Reported duration is less than one week; self-categorized by the patient as a rash; the patient also reports joint pain, fatigue and fever; reported lesion symptoms include bothersome appearance; Fitzpatrick skin type II; this is a close-up image; texture is reported as flat; the leg is involved: 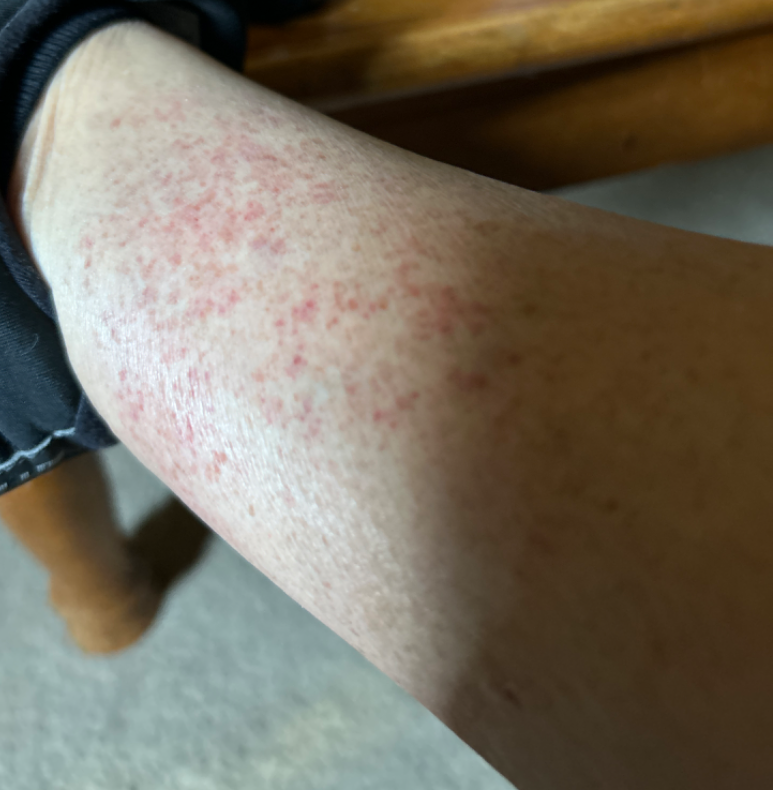| key | value |
|---|---|
| diagnostic considerations | the primary impression is Leukocytoclastic Vasculitis |